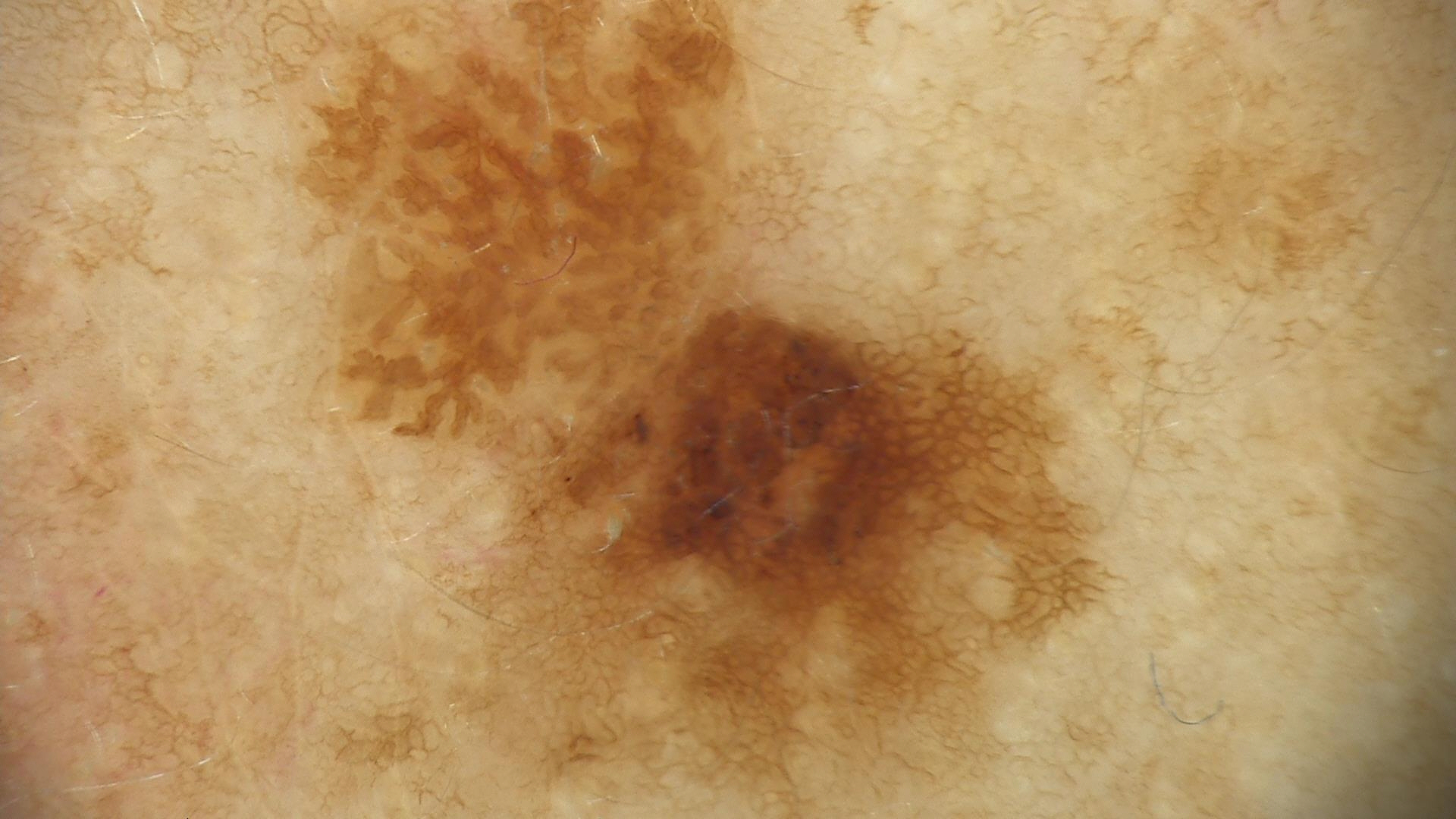Dermoscopy of a skin lesion.
The architecture is that of a keratinocytic lesion.
Diagnosed as a seborrheic keratosis.